A female patient, aged approximately 55; a dermoscopic close-up of a skin lesion — 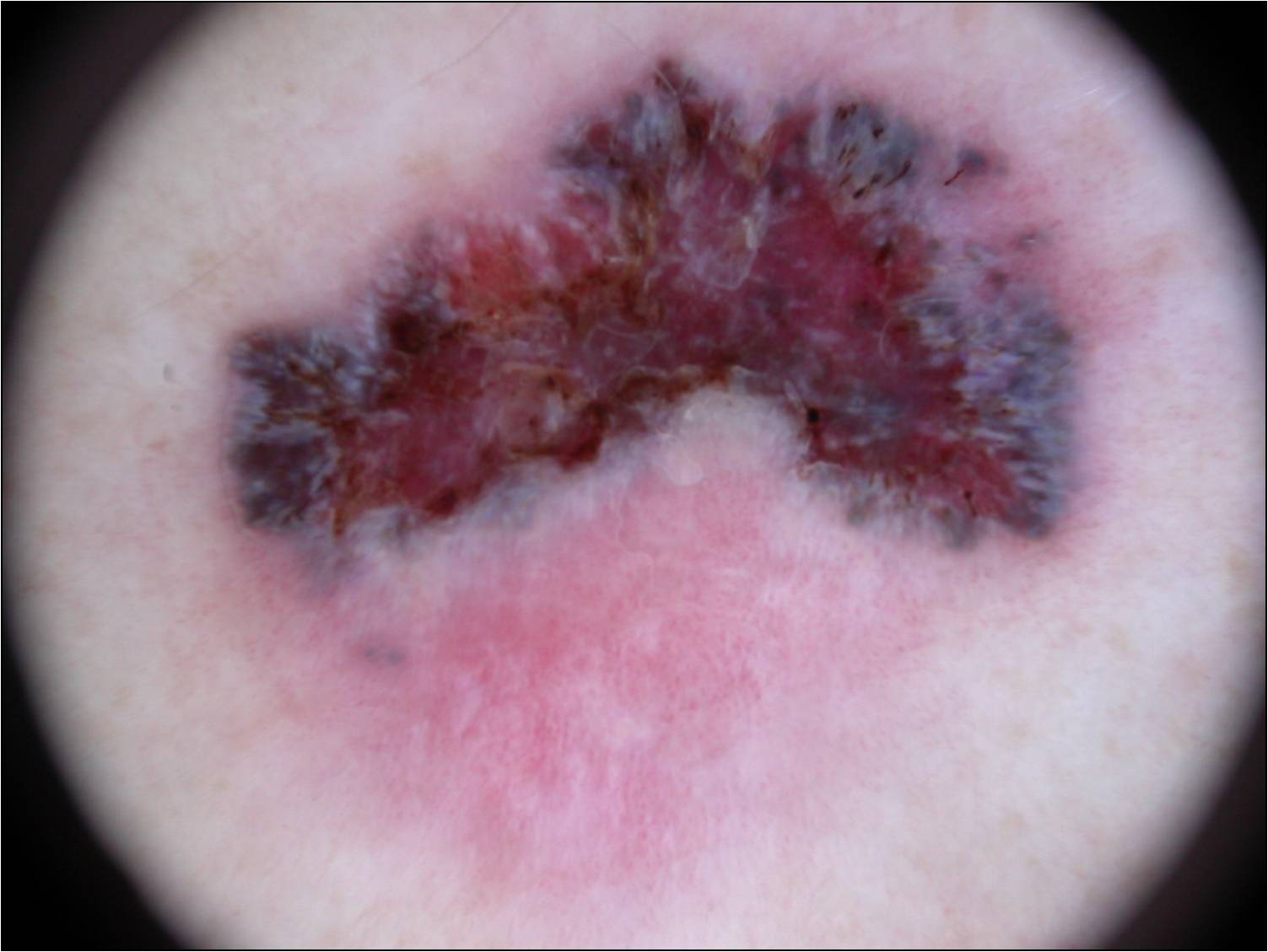| feature | finding |
|---|---|
| location | [208,19,1156,933] |
| dermoscopic features assessed but absent | globules, streaks, milia-like cysts, negative network, and pigment network |
| assessment | a melanoma, a malignant skin lesion |